The photo was captured at a distance · male patient, age 18–29:
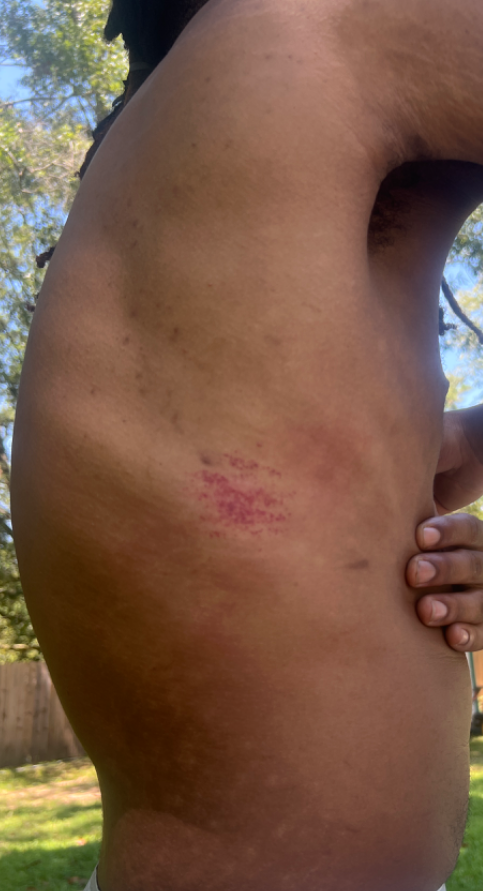Impression: The reviewing dermatologists' impression was: Leukocytoclastic Vasculitis and Purpura were considered with similar weight.